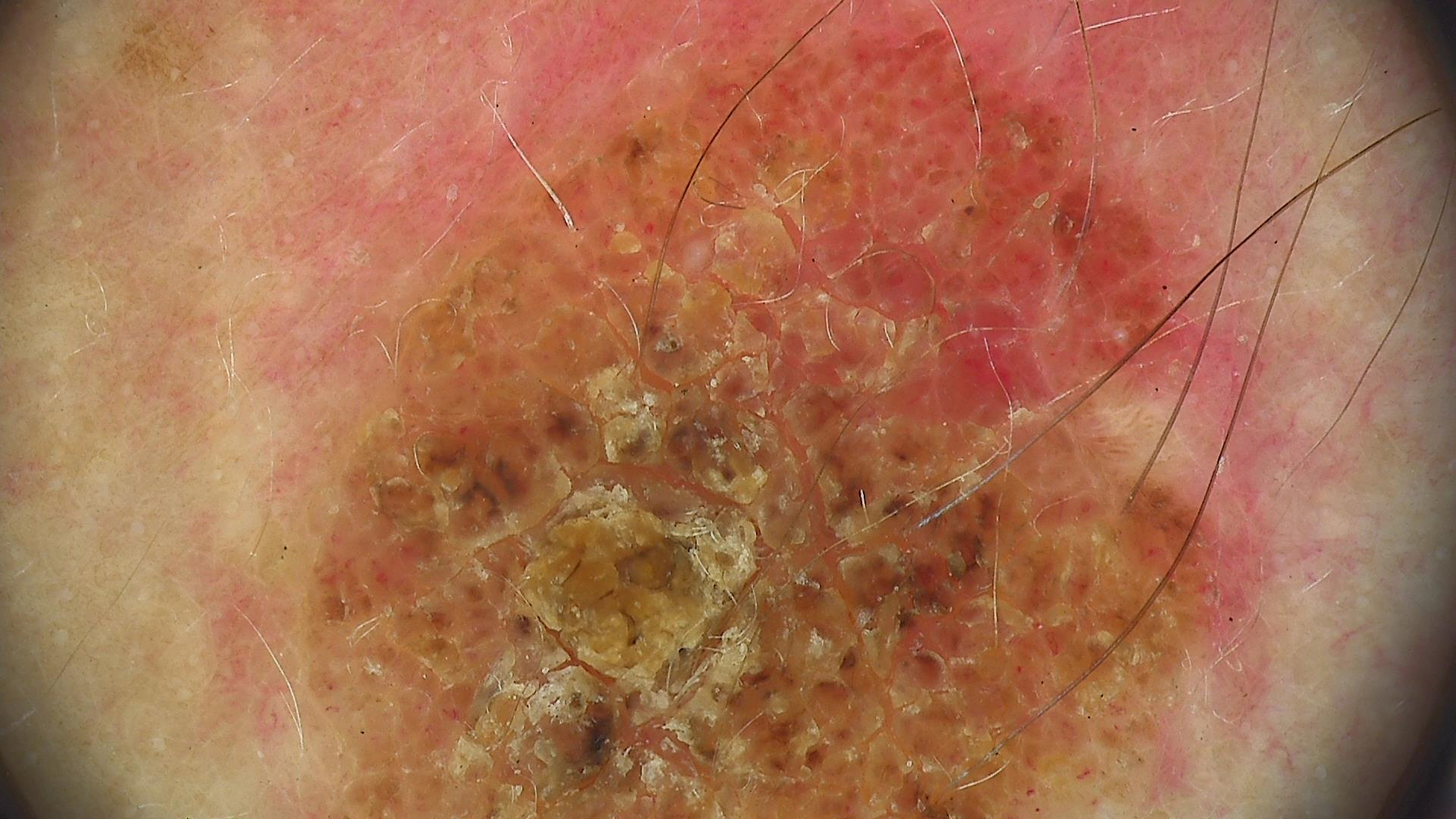• label · dermal nevus (expert consensus)